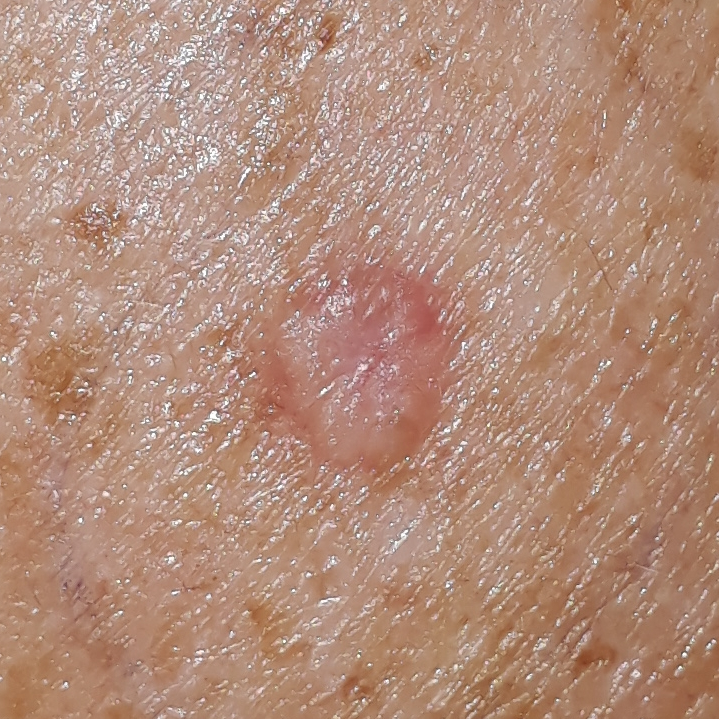Q: Tell me about the patient.
A: female, aged 54
Q: What is the patient's skin type?
A: II
Q: Where on the body is the lesion?
A: the chest
Q: Lesion size?
A: approx. 7 × 5 mm
Q: What is the diagnosis?
A: basal cell carcinoma (biopsy-proven)